The photograph was taken at a distance. The contributor is 18–29, male. The leg is involved — 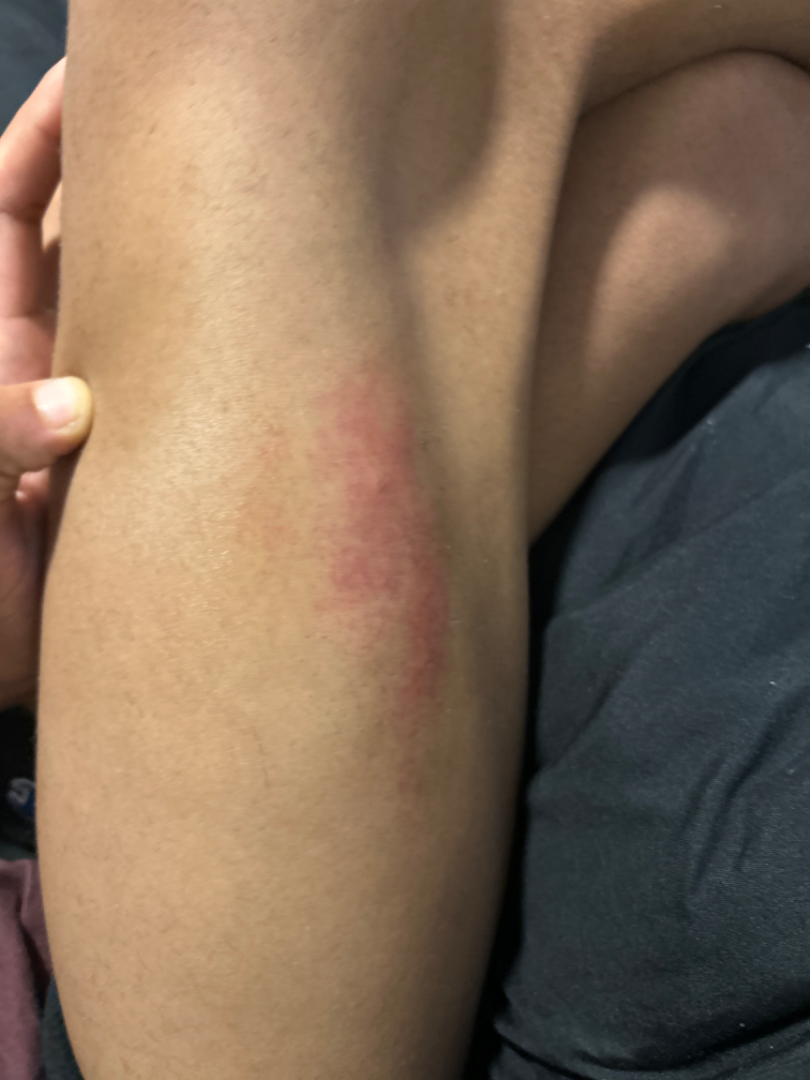Reviewed remotely by three dermatologists: Insect Bite; ecchymoses; and Acute dermatitis, NOS were each considered, in no particular order; less likely is Irritant Contact Dermatitis.